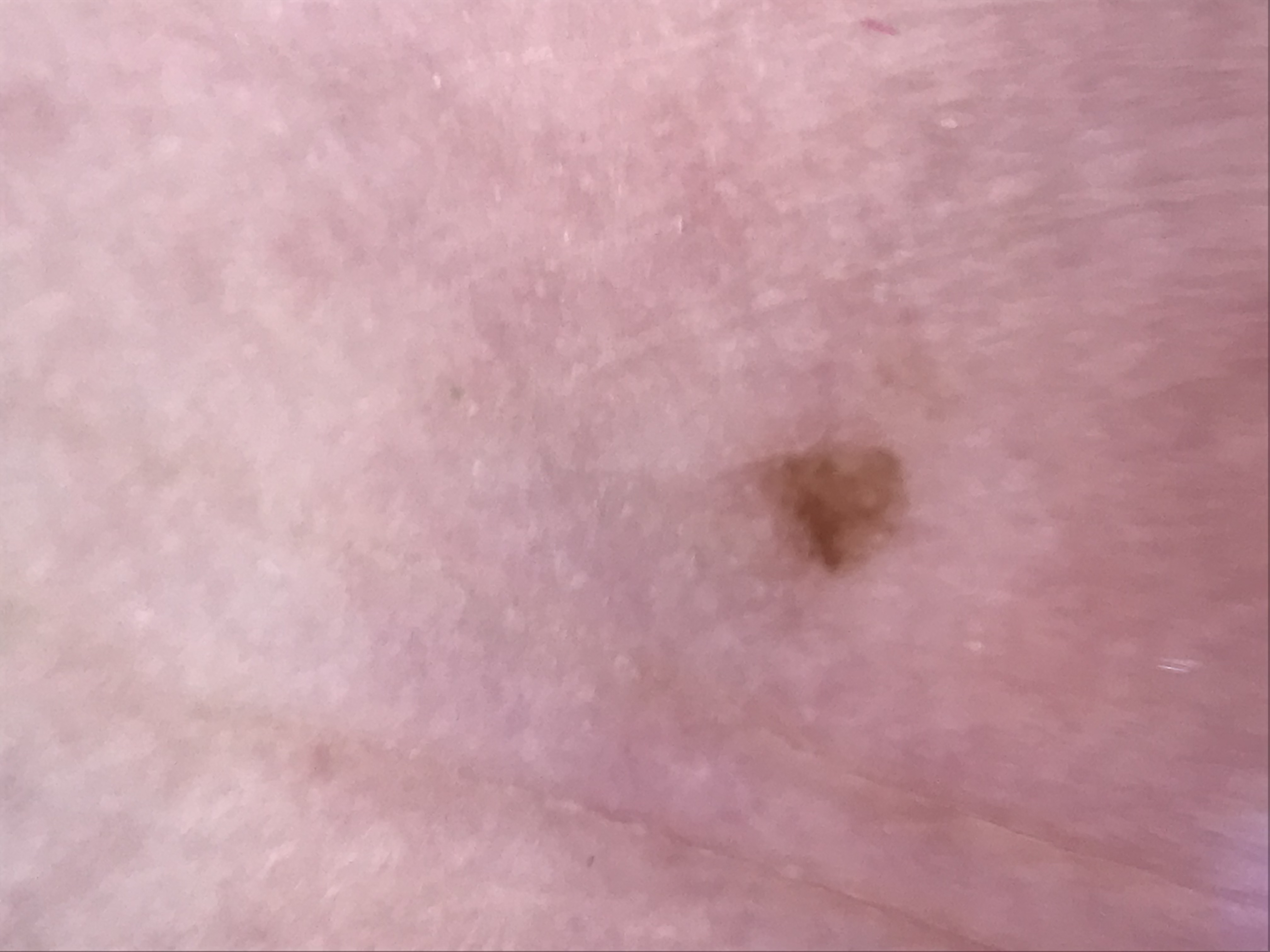Findings:
- diagnosis — acral junctional nevus (expert consensus)